The lesion involves the back of the torso; the photo was captured at an angle; symptoms reported: itching; the patient considered this a rash:
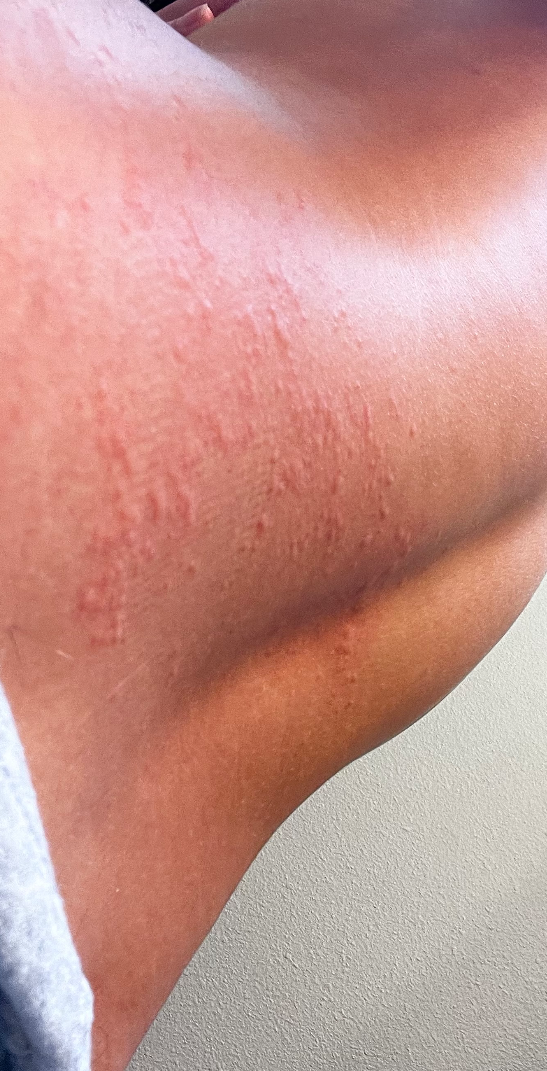clinical impression: the favored diagnosis is Urticaria; possibly Allergic Contact Dermatitis.